A male subject aged around 20.
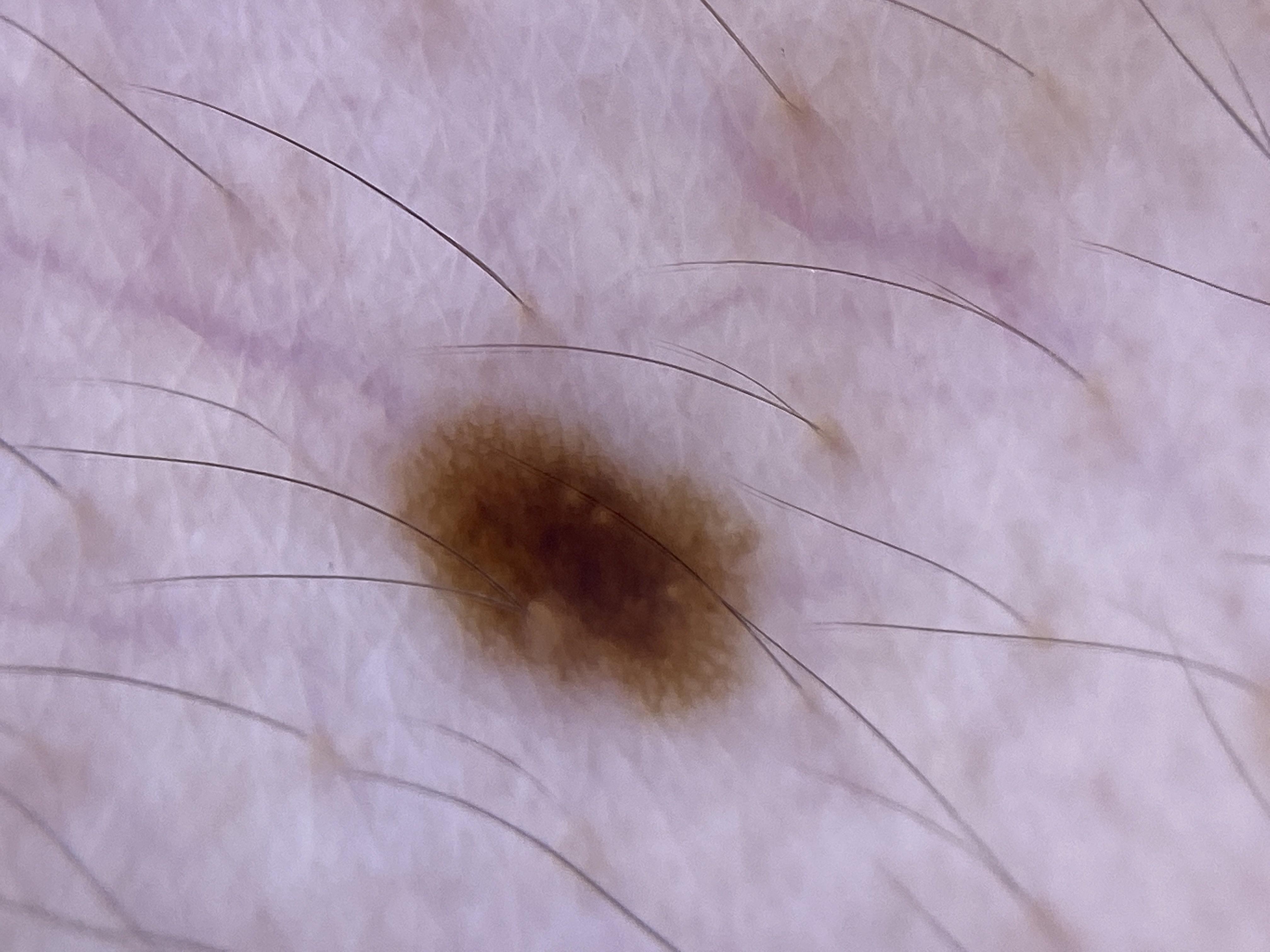Conclusion: Consistent with a melanocytic lesion — a nevus.